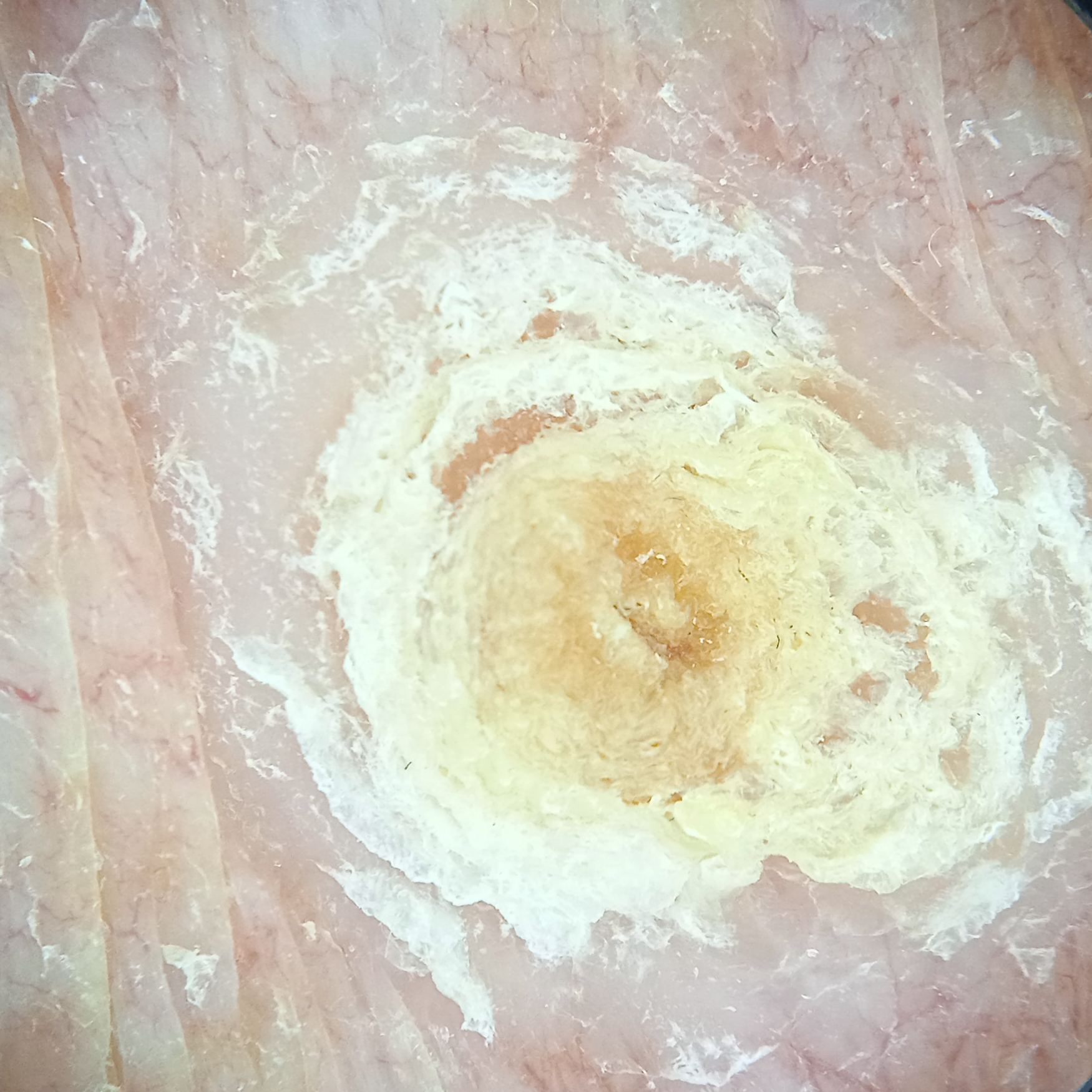referral=research study (no referral diagnosis); relevant history=a family history of skin cancer, a personal history of cancer; image type=dermoscopic image; patient=female, 92 years old; sun reaction=skin tans without first burning; body site=the torso; lesion size=12.5 mm; diagnostic label=squamous cell carcinoma (dermatologist consensus).